A dermatoscopic image of a skin lesion.
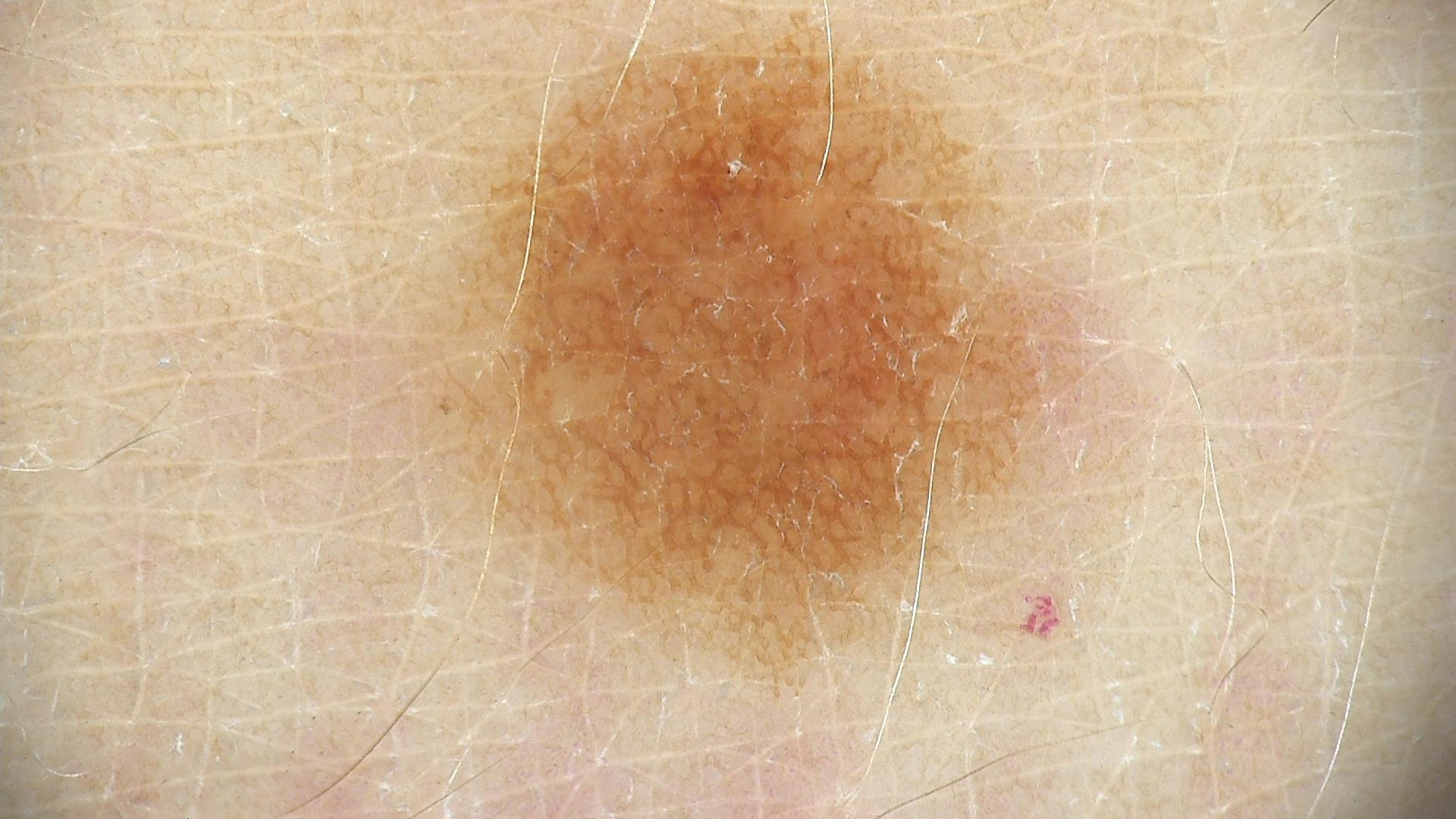subtype: banal | class: junctional nevus (expert consensus).